The back of the hand is involved · the photograph was taken at a distance · female contributor, age 40–49.
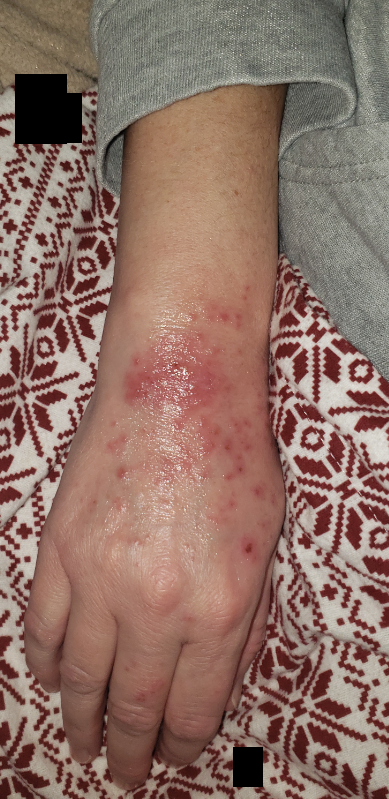Findings:
– diagnostic considerations: the differential is split between Allergic Contact Dermatitis and Herpes Simplex; less likely is Infected eczema